Dermoscopy of a skin lesion; on a questionnaire the patient reported no immunosuppression and no personal history of skin cancer; referred for assessment of suspected basal cell carcinoma: 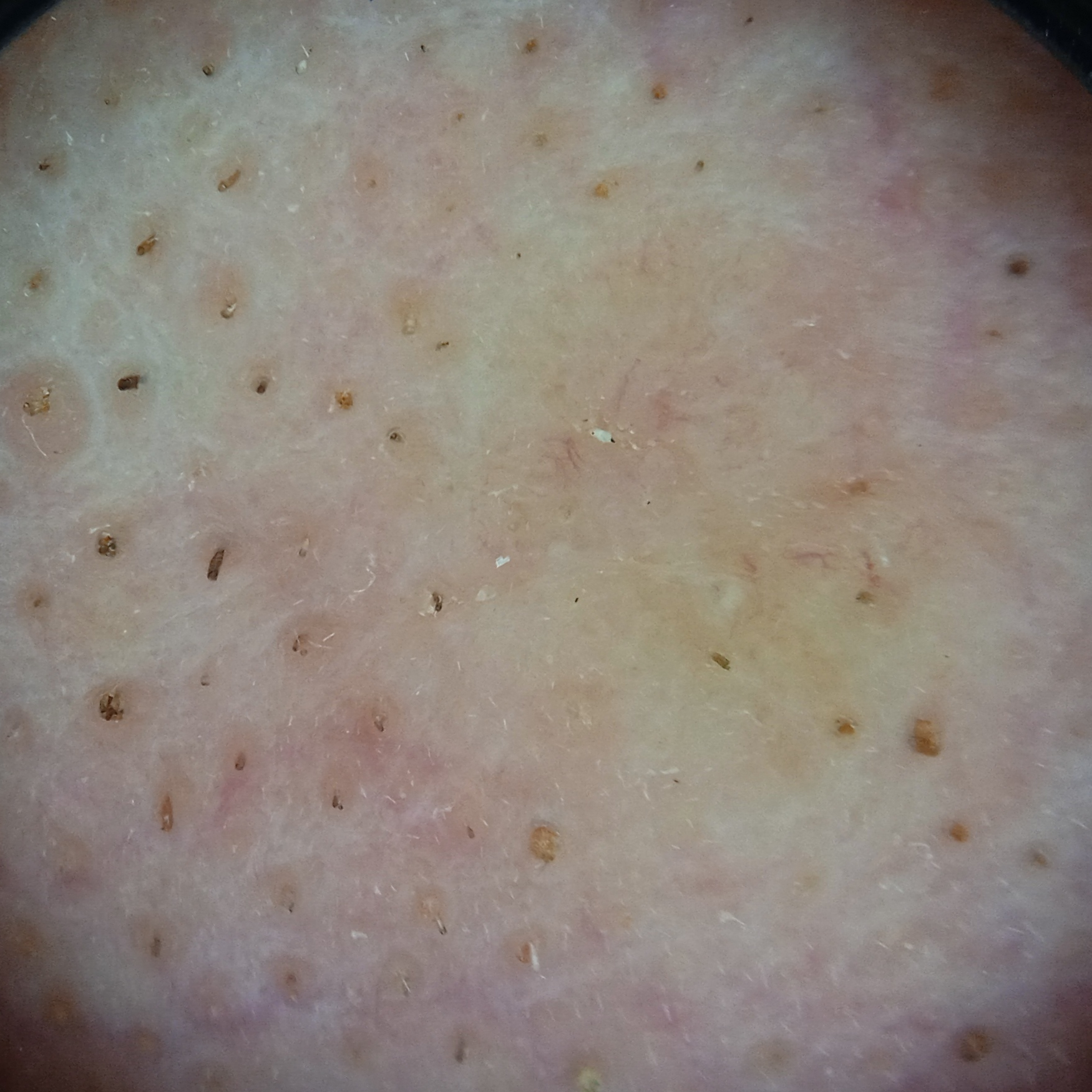| field | value |
|---|---|
| location | the face |
| size | 8.5 mm |
| diagnosis | basal cell carcinoma (biopsy-proven) |